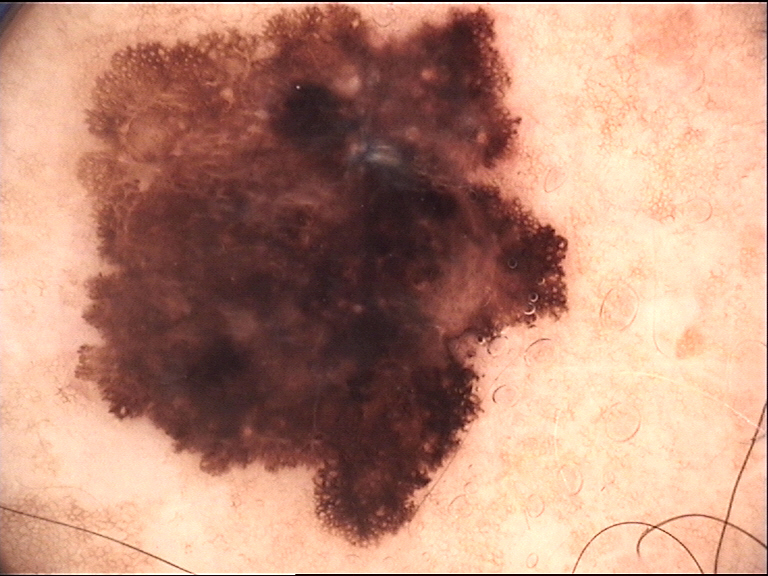{"diagnosis": {"name": "melanoma", "code": "mel", "malignancy": "malignant", "super_class": "melanocytic", "confirmation": "histopathology"}}